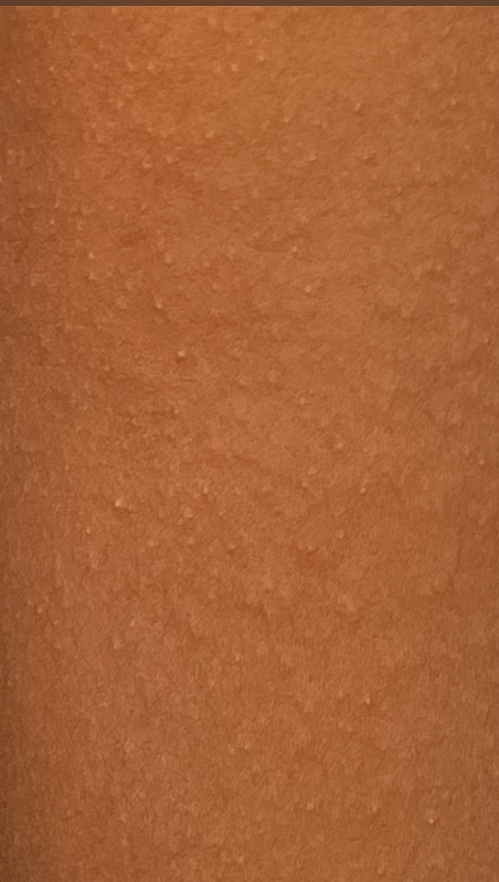Q: What was the assessment?
A: could not be assessed
Q: How was the photo taken?
A: close-up